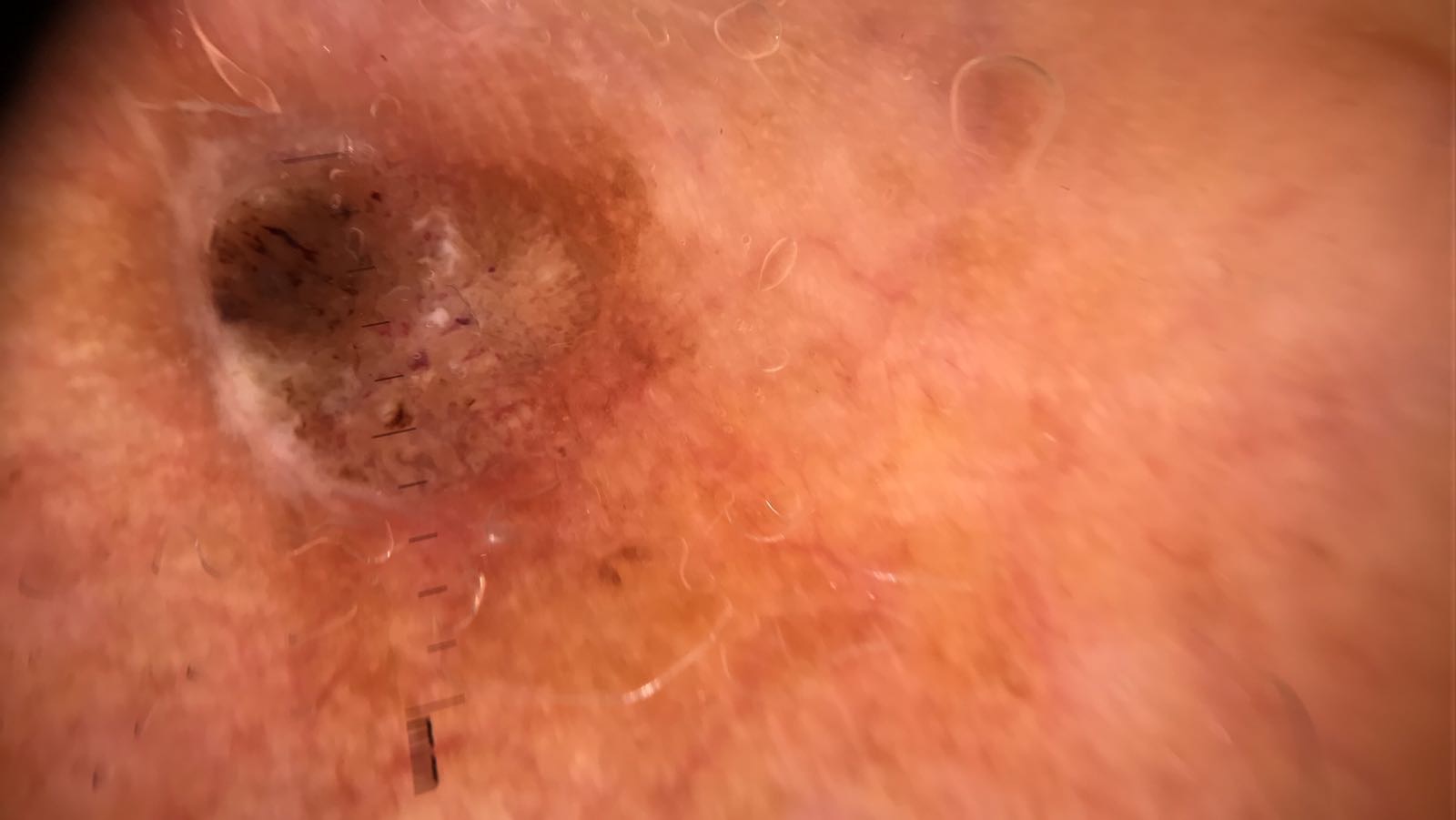Case: The architecture is that of a keratinocytic lesion. Impression: The diagnostic label was a seborrheic keratosis.